A male subject approximately 50 years of age. Recorded as FST II. A contact-polarized dermoscopy image of a skin lesion — 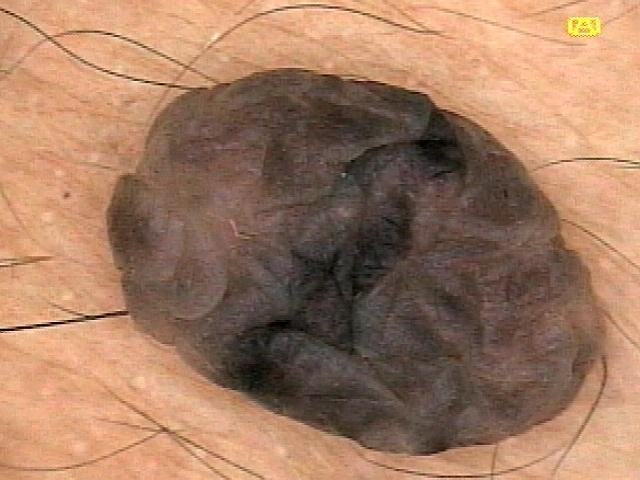Summary: Located on the trunk. Assessment: The clinical impression was a benign, melanocytic lesion — a nevus.